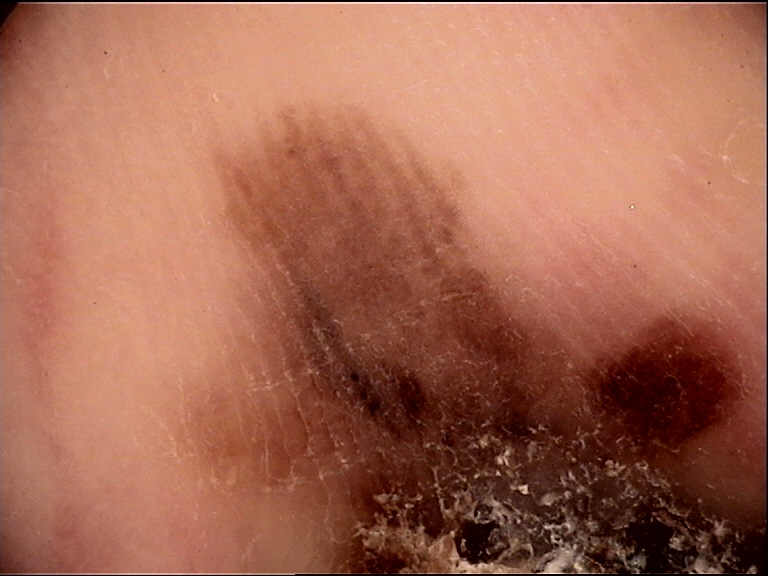Case:
- pathology — acral lentiginous melanoma (biopsy-proven)